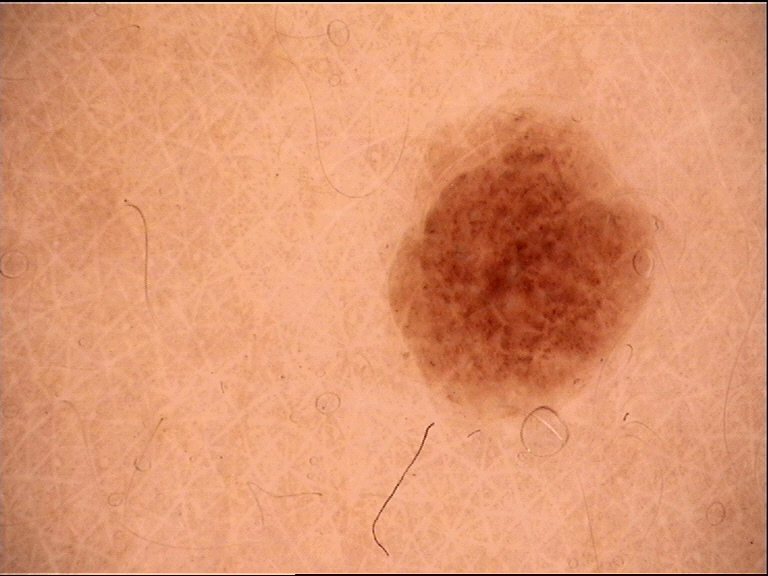Findings:
– classification · banal
– diagnosis · compound nevus (expert consensus)